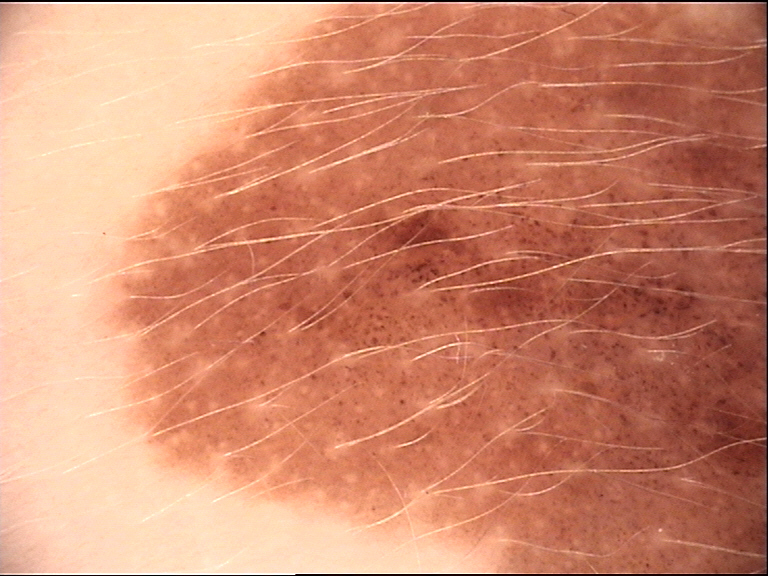<lesion>
<image>dermatoscopy</image>
<lesion_type>
<main_class>banal</main_class>
<pattern>junctional</pattern>
</lesion_type>
<diagnosis>
<name>congenital junctional nevus</name>
<code>cjb</code>
<malignancy>benign</malignancy>
<super_class>melanocytic</super_class>
<confirmation>expert consensus</confirmation>
</diagnosis>
</lesion>